A dermoscopic close-up of a skin lesion.
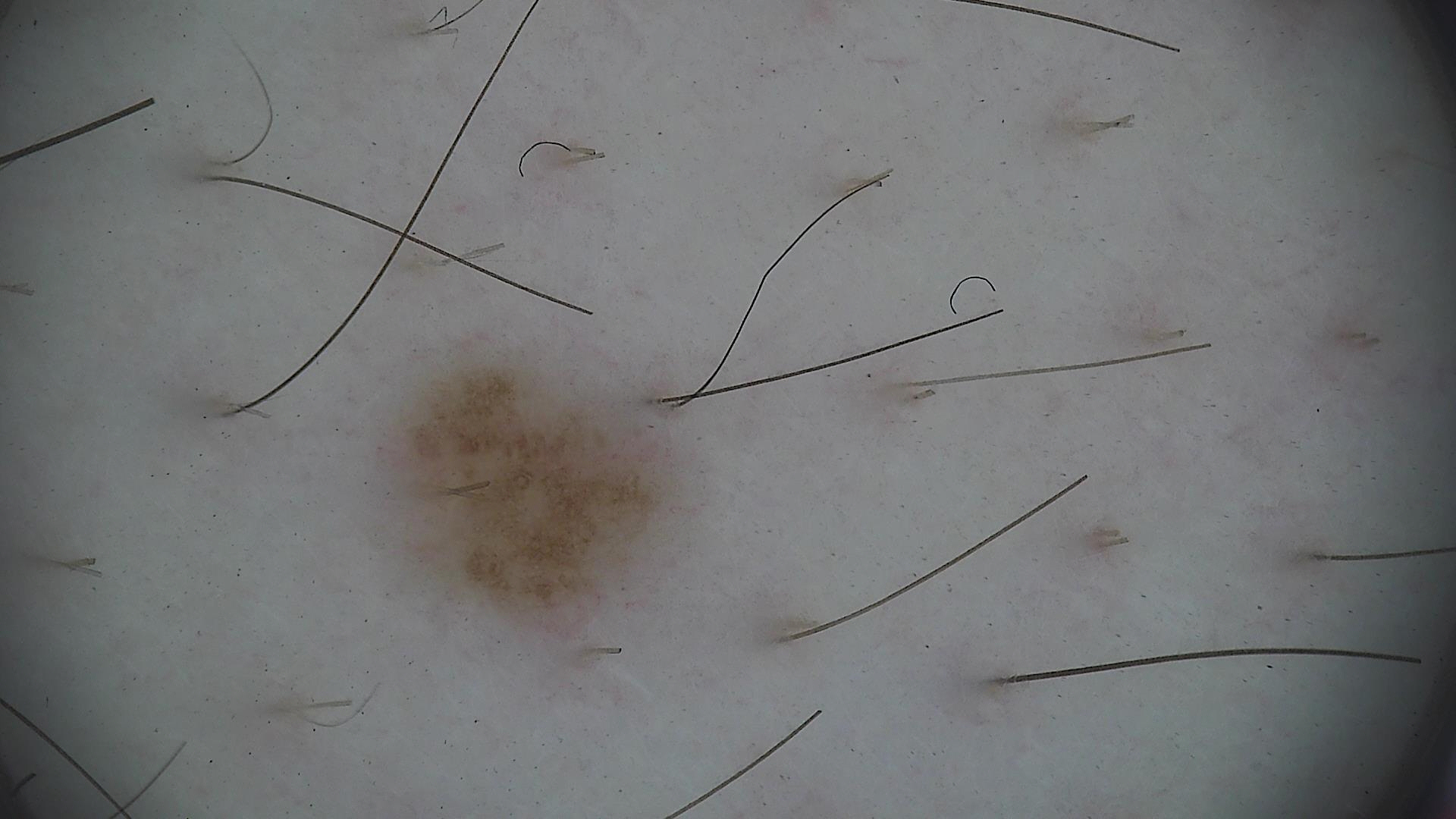Conclusion: Classified as a benign lesion — a dysplastic junctional nevus.